History notes no pesticide exposure. A female subject 65 years of age. Fitzpatrick phototype II. A clinical close-up photograph of a skin lesion: 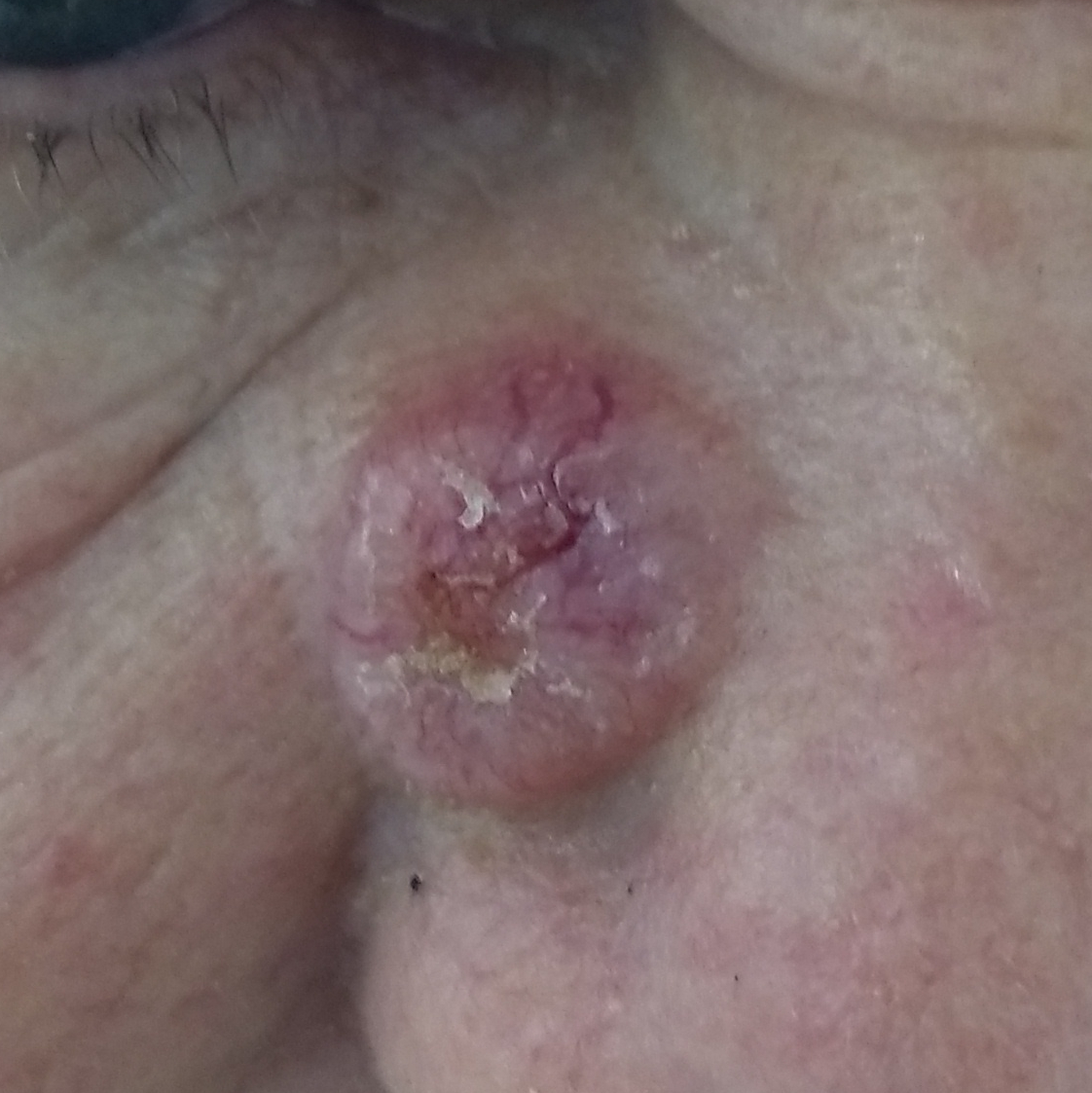Case:
– site · the nose
– lesion diameter · approx. 13 × 10 mm
– patient-reported symptoms · bleeding, growth, elevation, change in appearance / no pain, no itching
– diagnostic label · basal cell carcinoma (biopsy-proven)